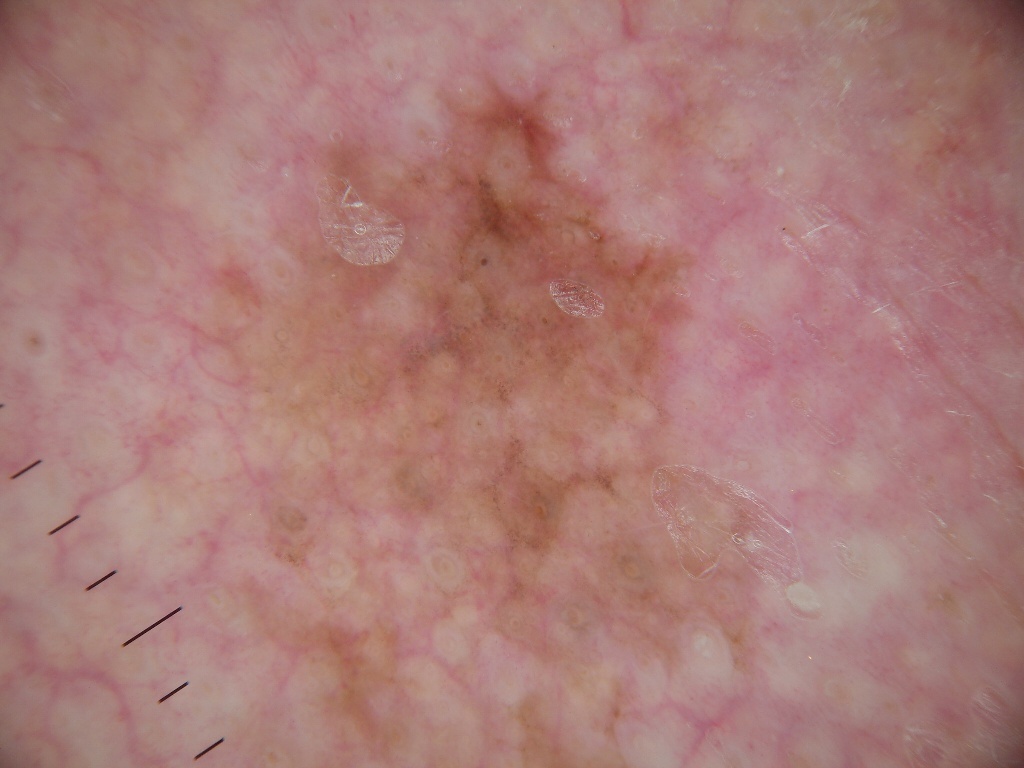Q: What kind of image is this?
A: dermatoscopic image of a skin lesion
Q: Where is the lesion in the image?
A: x1=188, y1=60, x2=792, y2=766
Q: What did the assessment conclude?
A: a malignant skin lesion